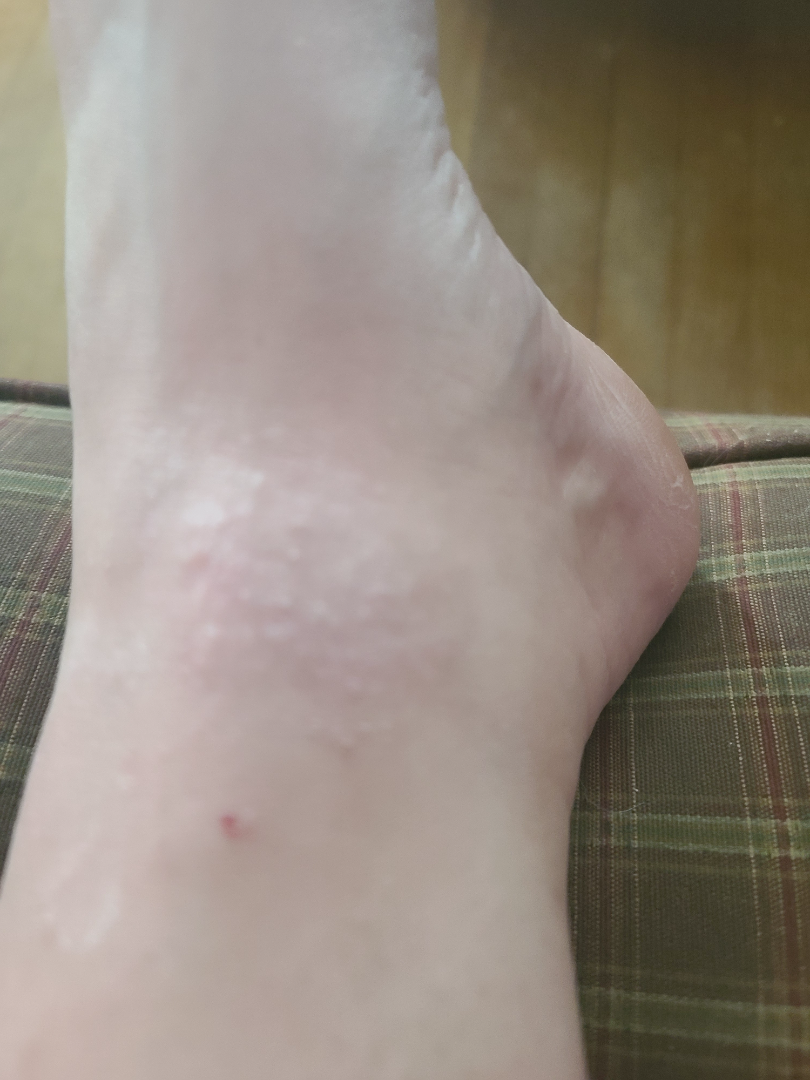Findings:
- assessment — ungradable on photographic review
- subject — female, age 18–29
- location — leg
- shot type — close-up